This image was taken at an angle · the patient is 18–29, female · the leg is involved: 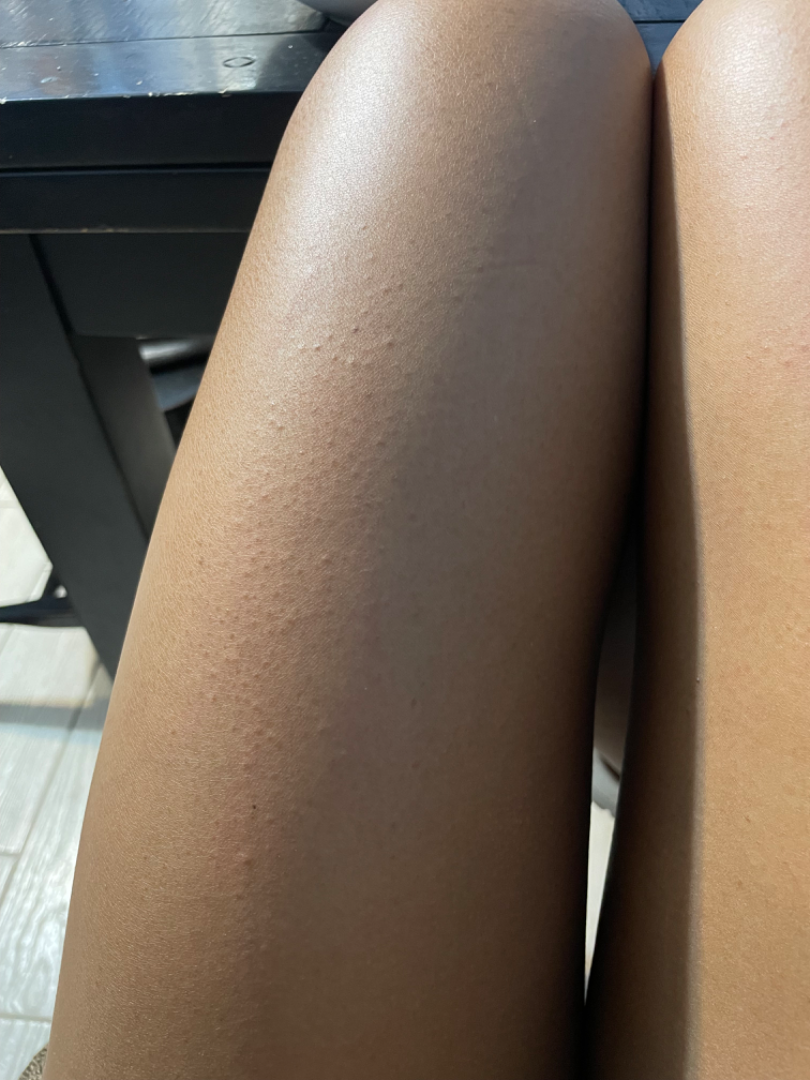| key | value |
|---|---|
| diagnostic considerations | three dermatologists each reviewed the case: the primary impression is Keratosis pilaris; possibly Eczema |